Skin type II · a female subject aged 68-72 — 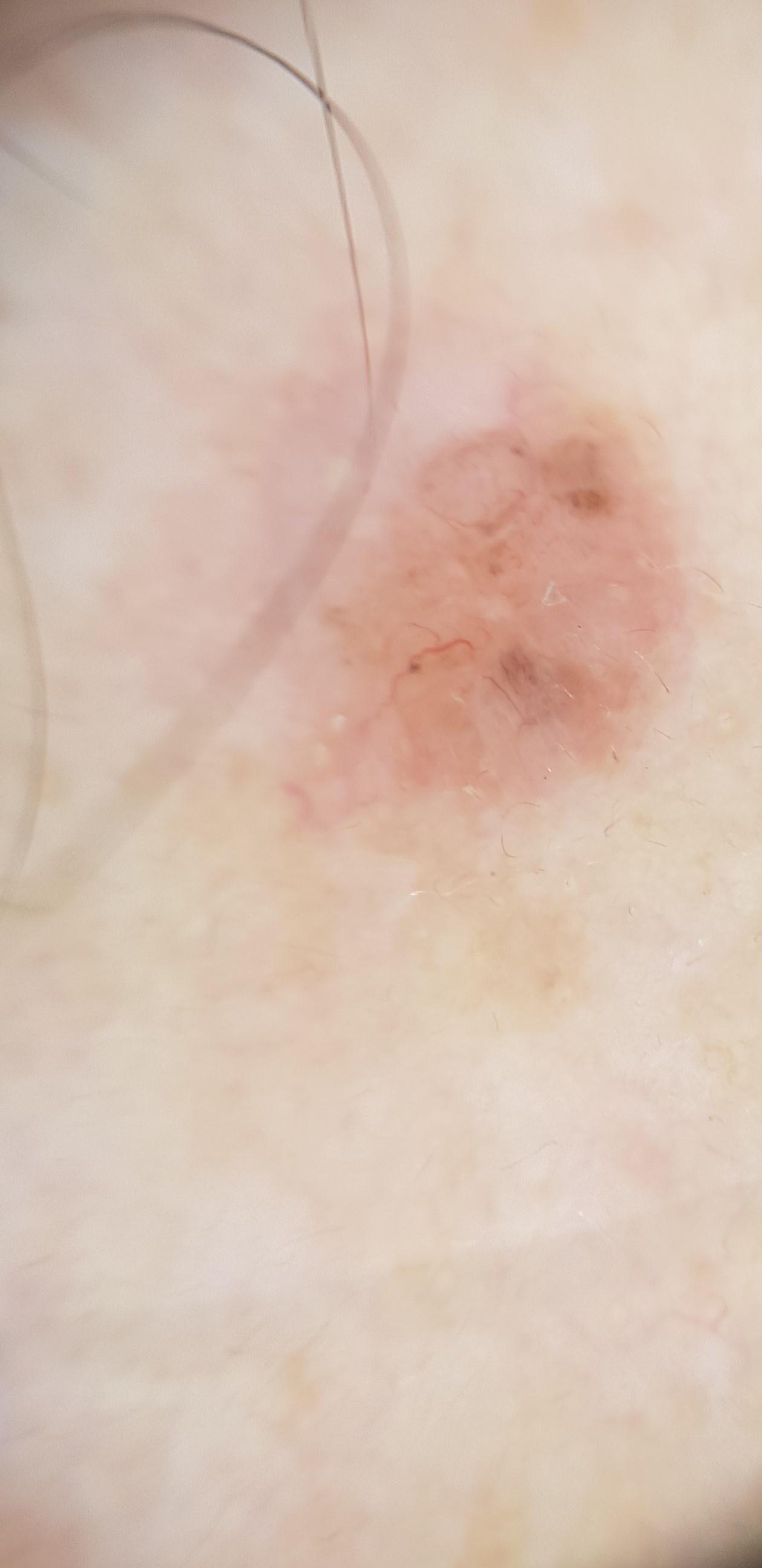{
  "diagnosis": {
    "name": "Basal cell carcinoma",
    "malignancy": "malignant",
    "confirmation": "histopathology",
    "lineage": "adnexal"
  }
}